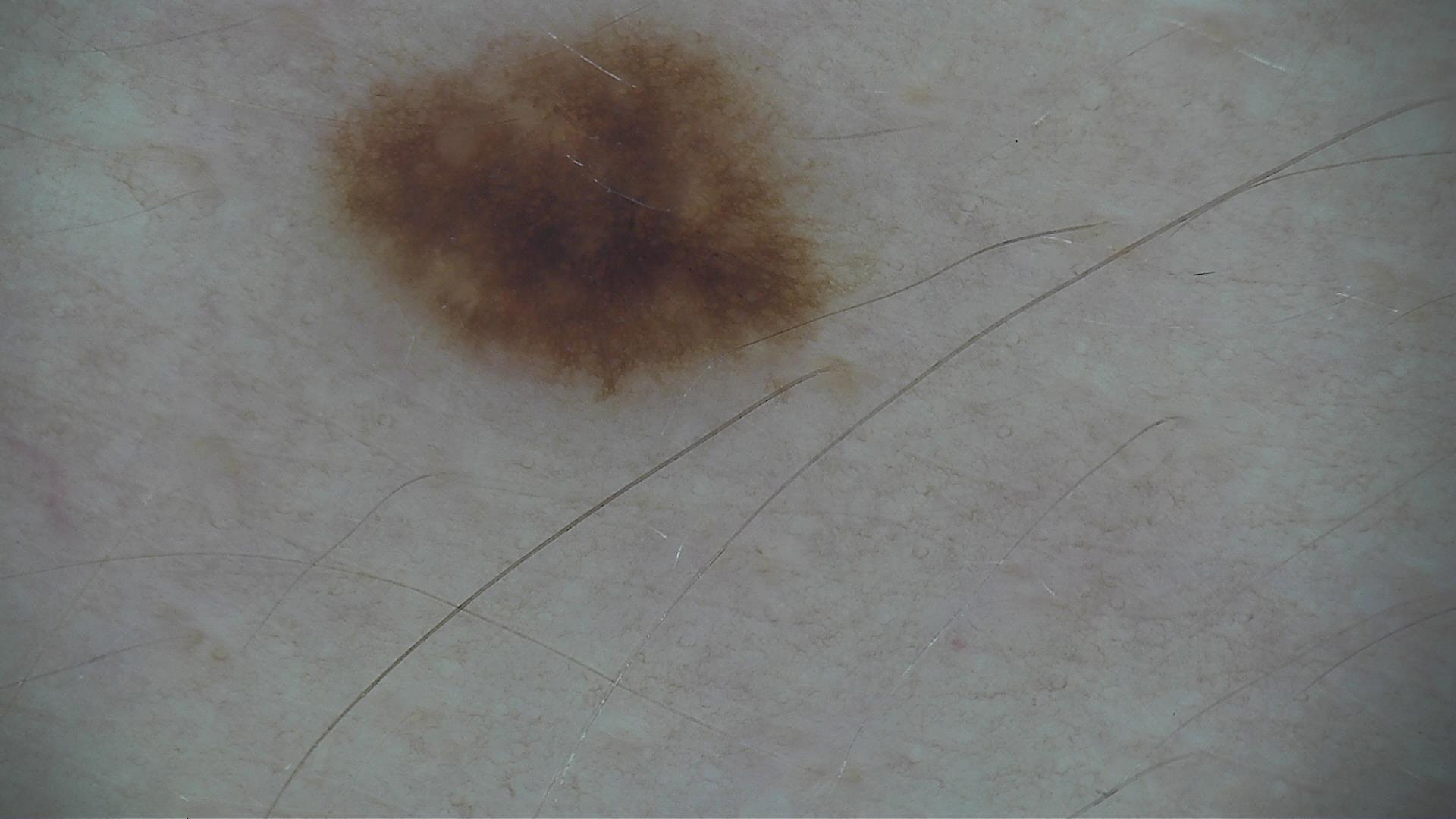A dermoscopy image of a single skin lesion. The diagnosis was a dysplastic junctional nevus.